The contributor is 70–79, female · the lesion involves the leg · self-categorized by the patient as a rash · the condition has been present for one to four weeks · the patient notes the lesion is raised or bumpy · this image was taken at an angle:
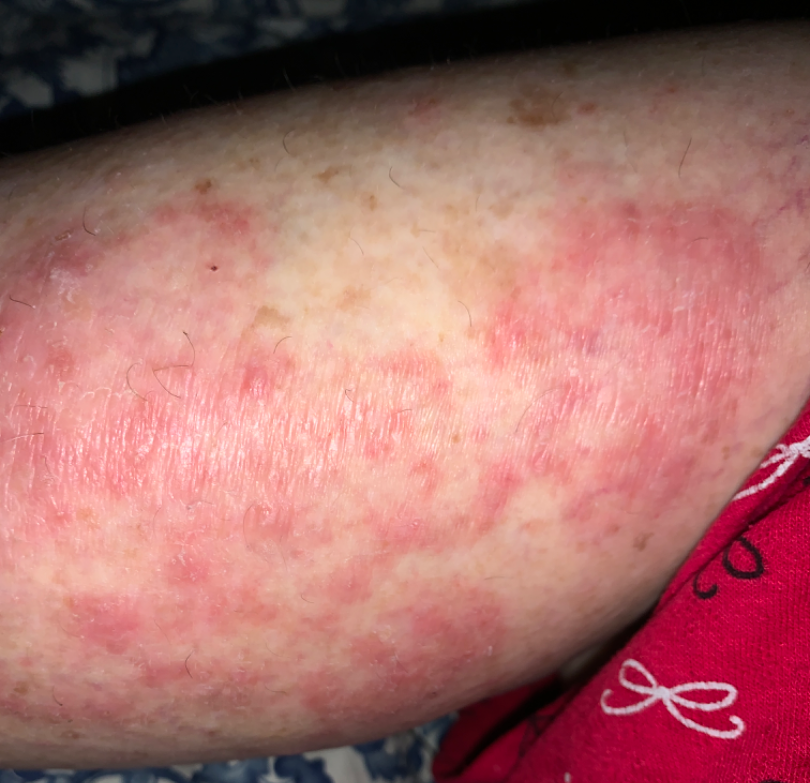Impression:
Reviewed remotely by one dermatologist: most consistent with Tinea; also raised was Psoriasis; with consideration of Eczema.